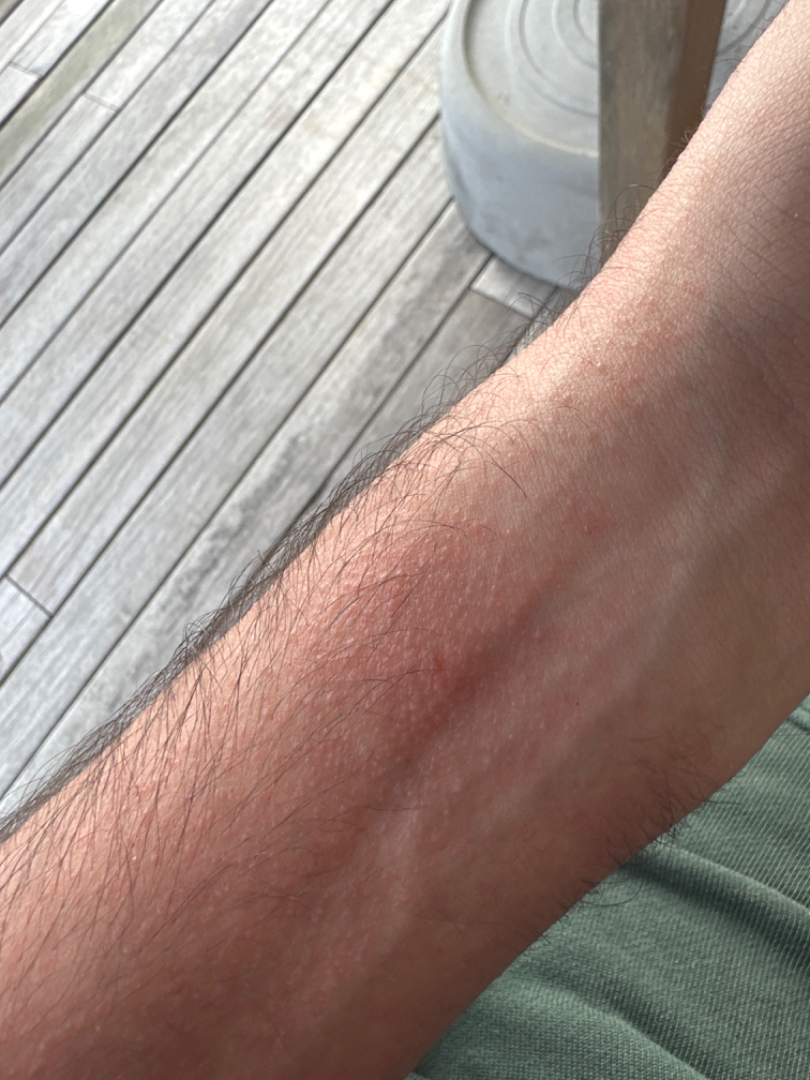Notes:
– diagnostic considerations — one reviewing dermatologist: most consistent with Eczema